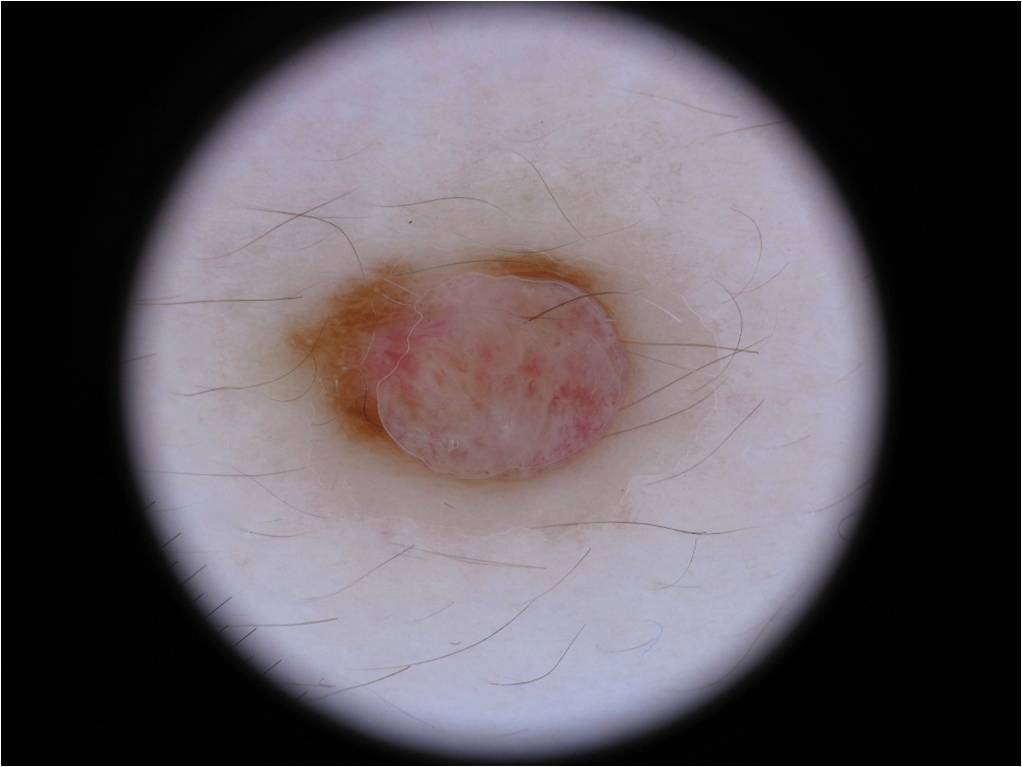This is a dermoscopic photograph of a skin lesion. A male subject, aged around 25. The lesion spans box(276, 247, 643, 496). Dermoscopic assessment notes pigment network and negative network, with no milia-like cysts, streaks, or globules. Consistent with a melanocytic nevus.